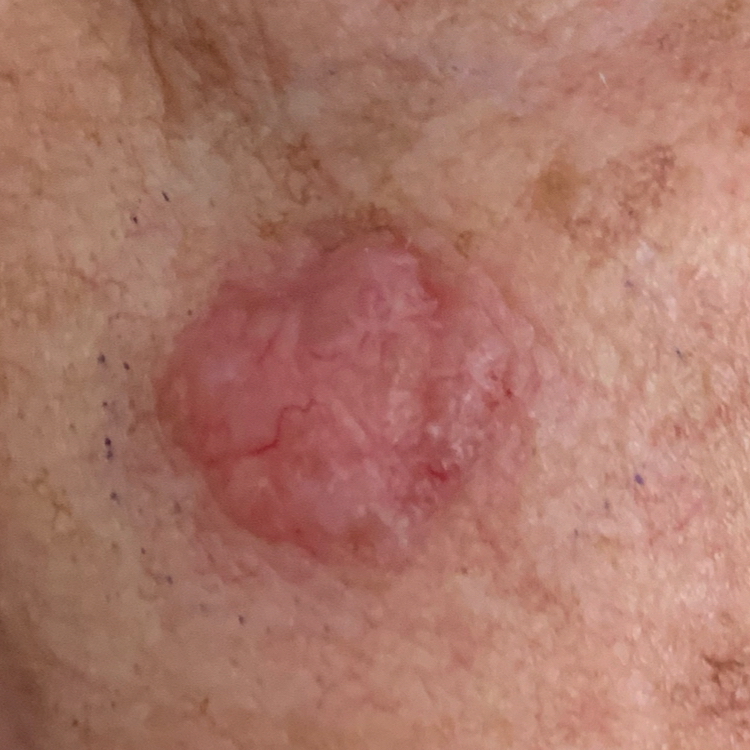{
  "image": "clinical photo",
  "symptoms": {
    "present": [
      "growth",
      "itching",
      "elevation"
    ]
  },
  "diagnosis": {
    "name": "basal cell carcinoma",
    "code": "BCC",
    "malignancy": "malignant",
    "confirmation": "histopathology"
  }
}